Located on the top or side of the foot, palm and arm; the contributor notes the condition has been present for more than one year; the lesion is associated with bothersome appearance and enlargement; the photograph was taken at an angle; the contributor is female; texture is reported as rough or flaky and raised or bumpy:
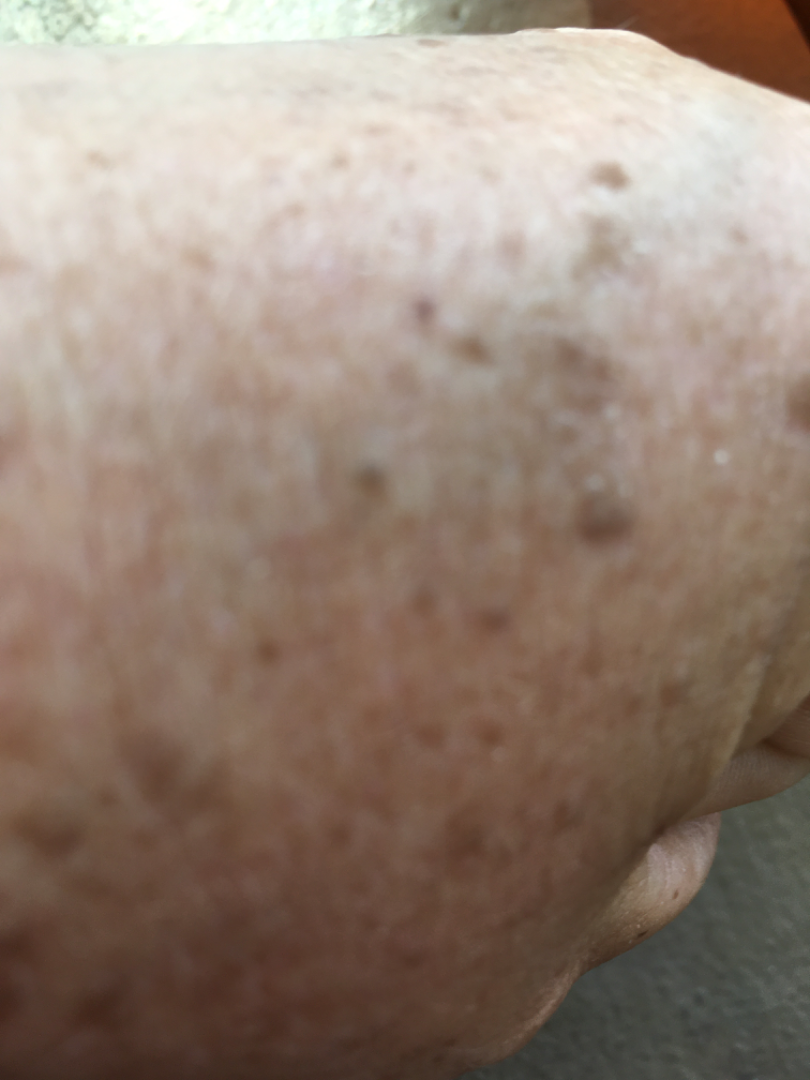Case summary:
- clinical impression — most likely SK/ISK; possibly Lentigo